The lesion involves the arm. The photograph was taken at an angle. The subject is 50–59, female.
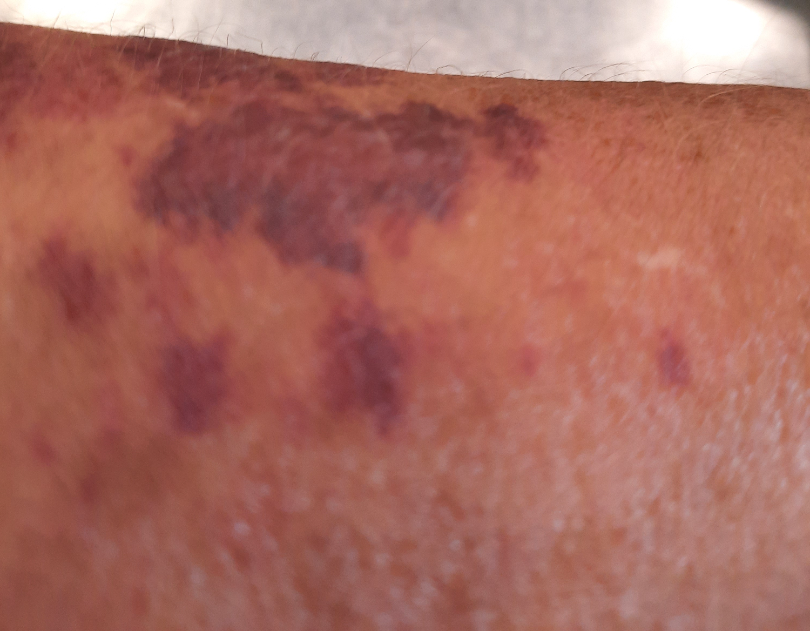Assessment: The primary impression is ecchymoses.